This image was taken at a distance. The affected area is the front of the torso, arm and leg. Female contributor, age 40–49.
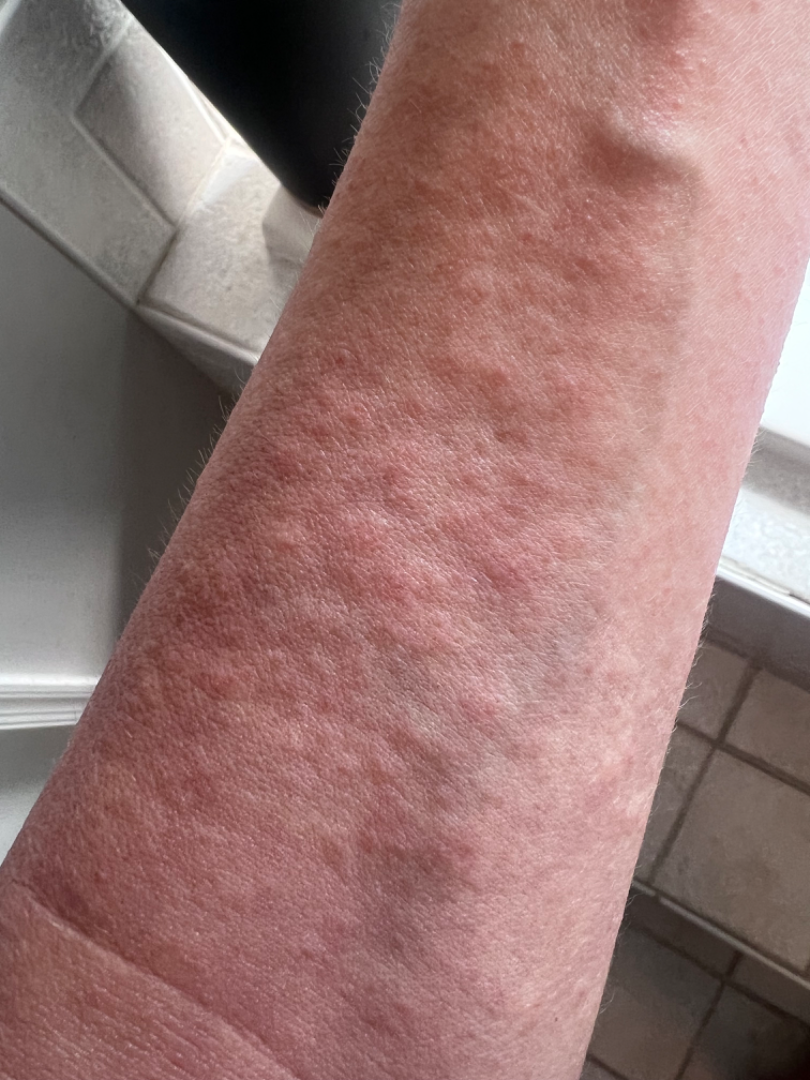On remote dermatologist review, Urticaria (most likely).